Self-categorized by the patient as a rash · the lesion is associated with darkening and itching · the condition has been present for one to four weeks · female subject, age 30–39 · the photo was captured at an angle · the affected area is the leg, front of the torso and back of the torso · no associated systemic symptoms reported:
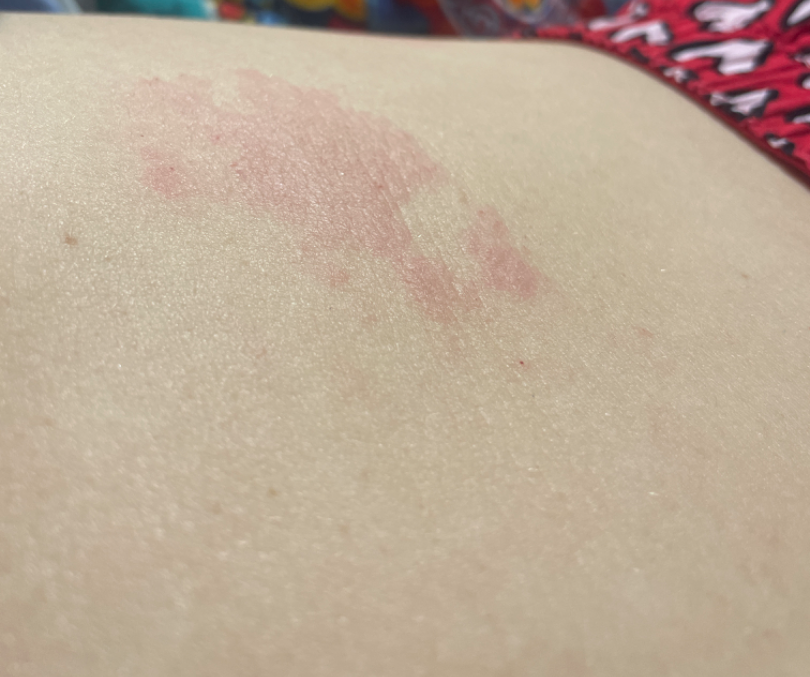differential diagnosis=most consistent with Herpes Zoster